The patient is 18–29, female. The arm is involved. This is a close-up image — 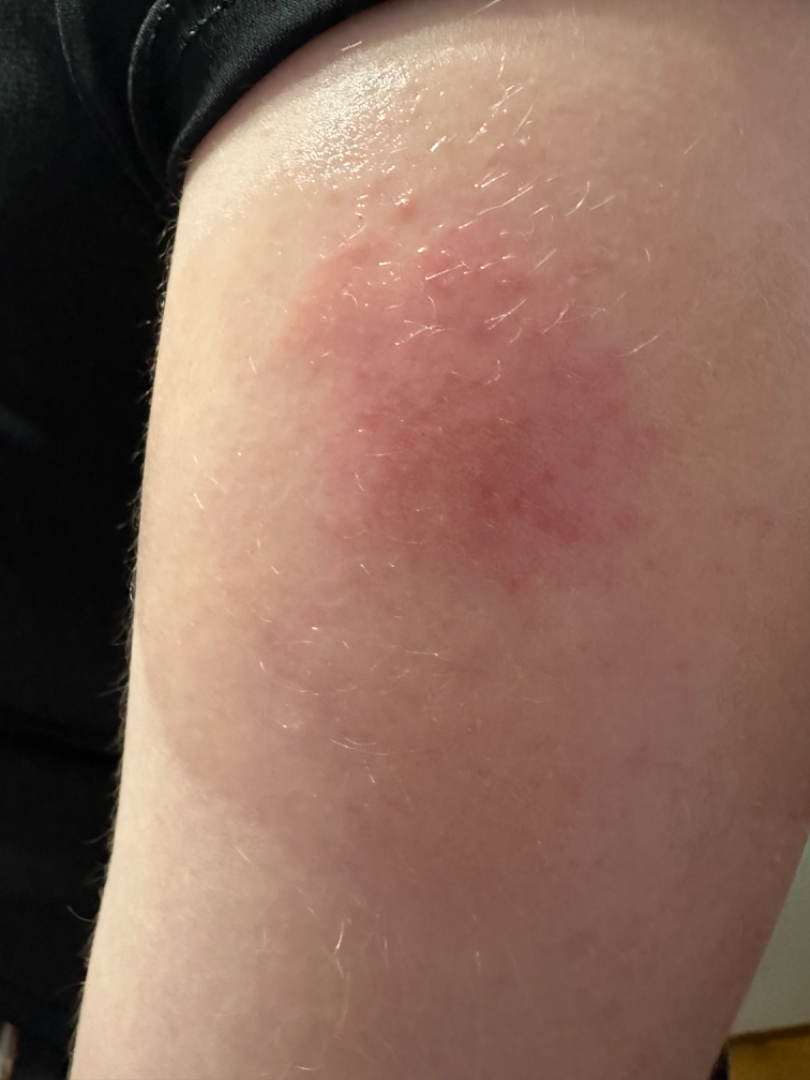<report>
  <texture>raised or bumpy</texture>
  <duration>about one day</duration>
  <systemic_symptoms>none reported</systemic_symptoms>
  <patient_category>a rash</patient_category>
  <symptoms>itching</symptoms>
  <differential>
    <Impetigo>0.33</Impetigo>
    <Injection site disorder>0.33</Injection site disorder>
    <Allergic Contact Dermatitis>0.33</Allergic Contact Dermatitis>
  </differential>
</report>